A subject in their 50s · a smartphone photograph of a skin lesion — 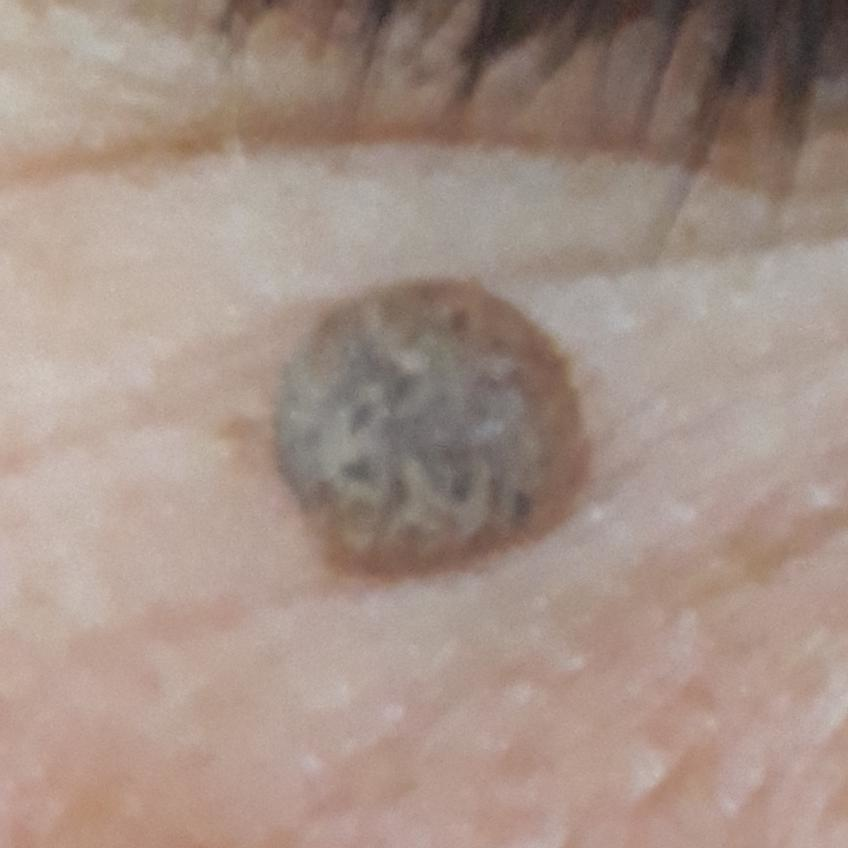- region · the face
- reported symptoms · growth, elevation
- impression · seborrheic keratosis (clinical consensus)